A dermatoscopic image of a skin lesion:
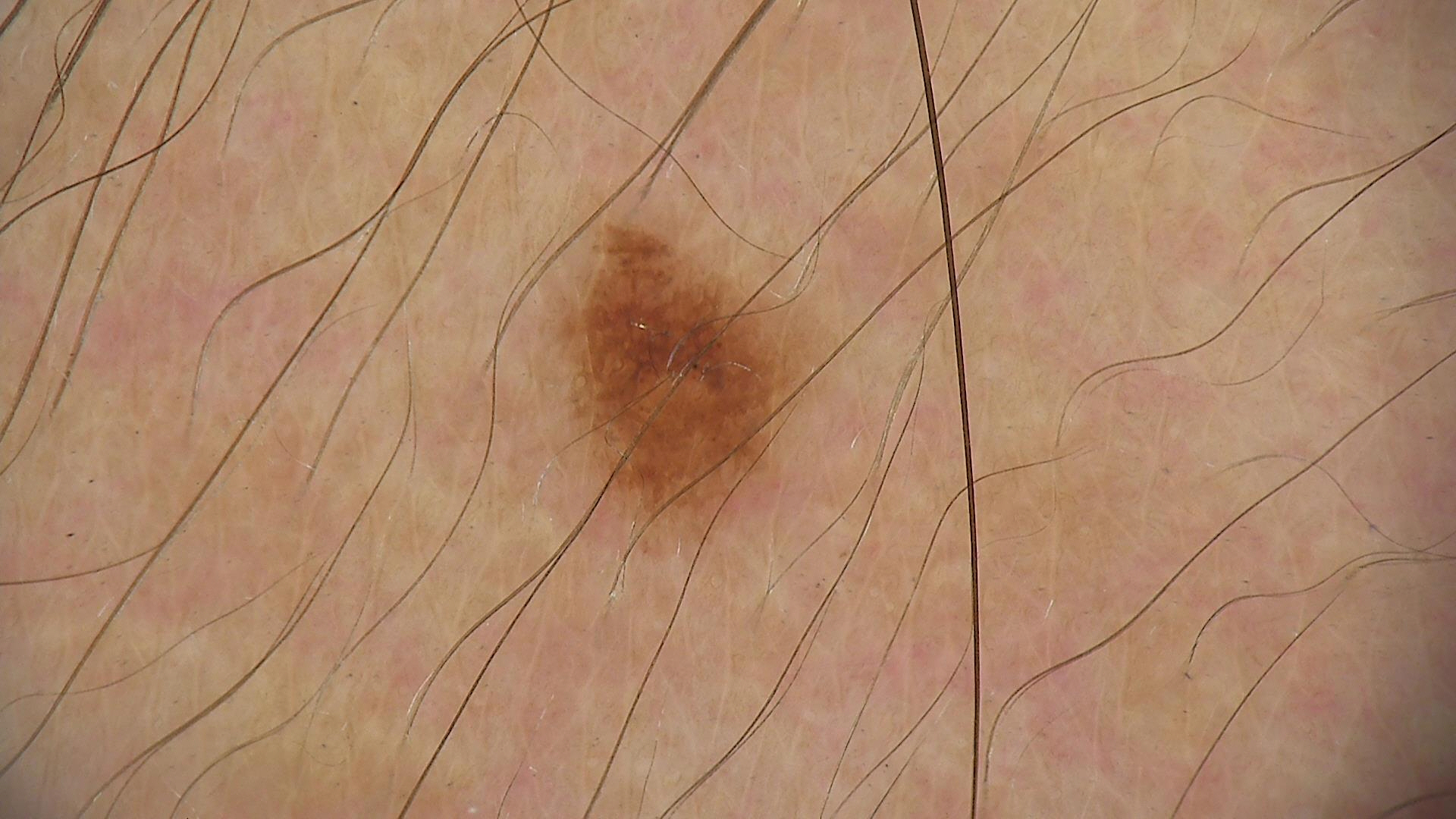Q: What was the diagnostic impression?
A: dysplastic junctional nevus (expert consensus)